Imaged for a research study, with no referral diagnosis recorded.
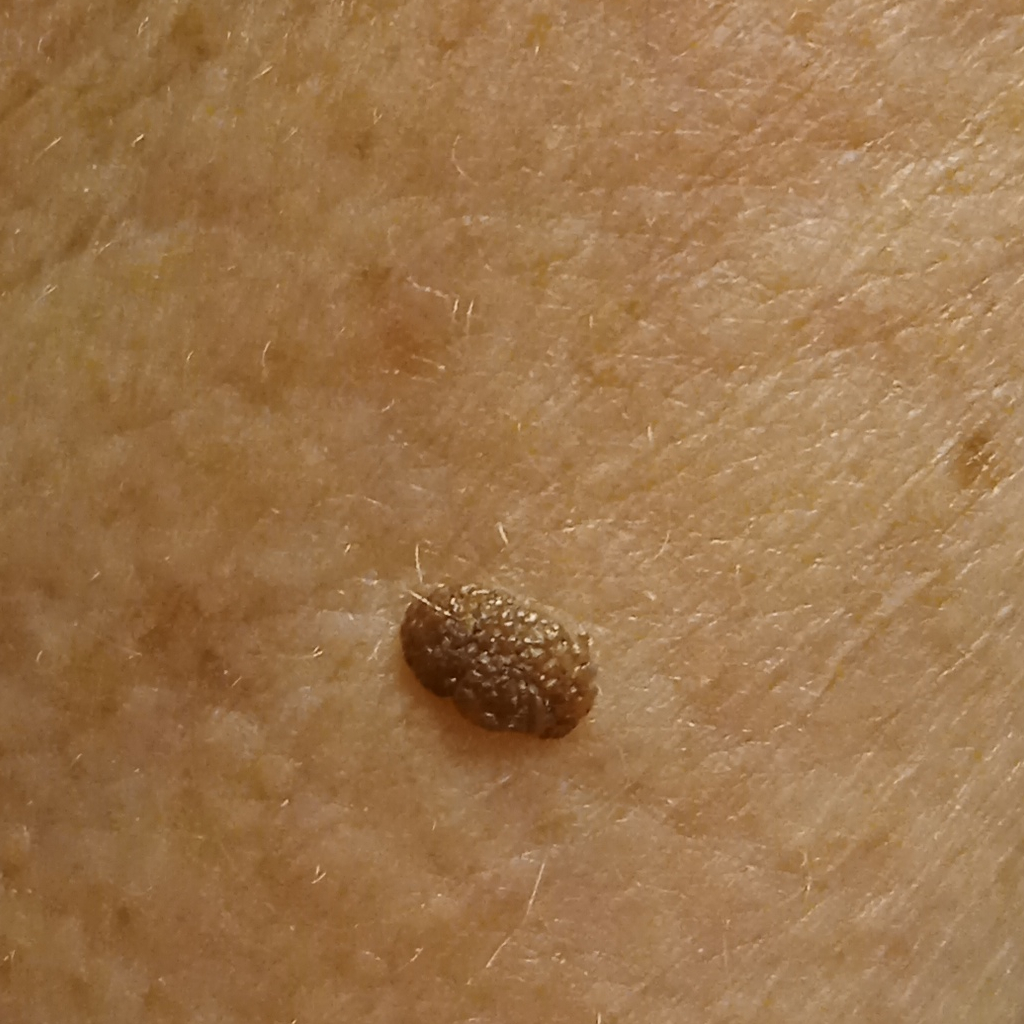location: an arm | assessment: seborrheic keratosis (dermatologist consensus).